The affected area is the back of the torso. Close-up view. The subject is a female aged 18–29.
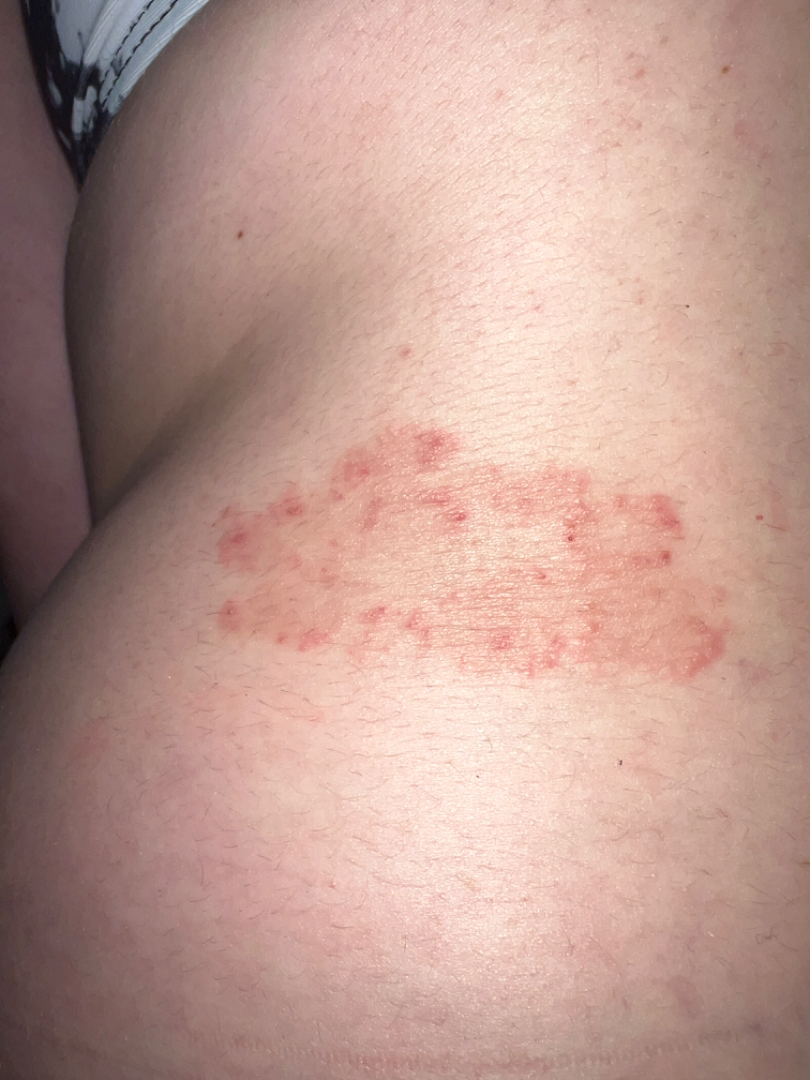The patient indicates the lesion is raised or bumpy.
Present for one to three months.
The patient considered this a rash.
Consistent with Tinea.